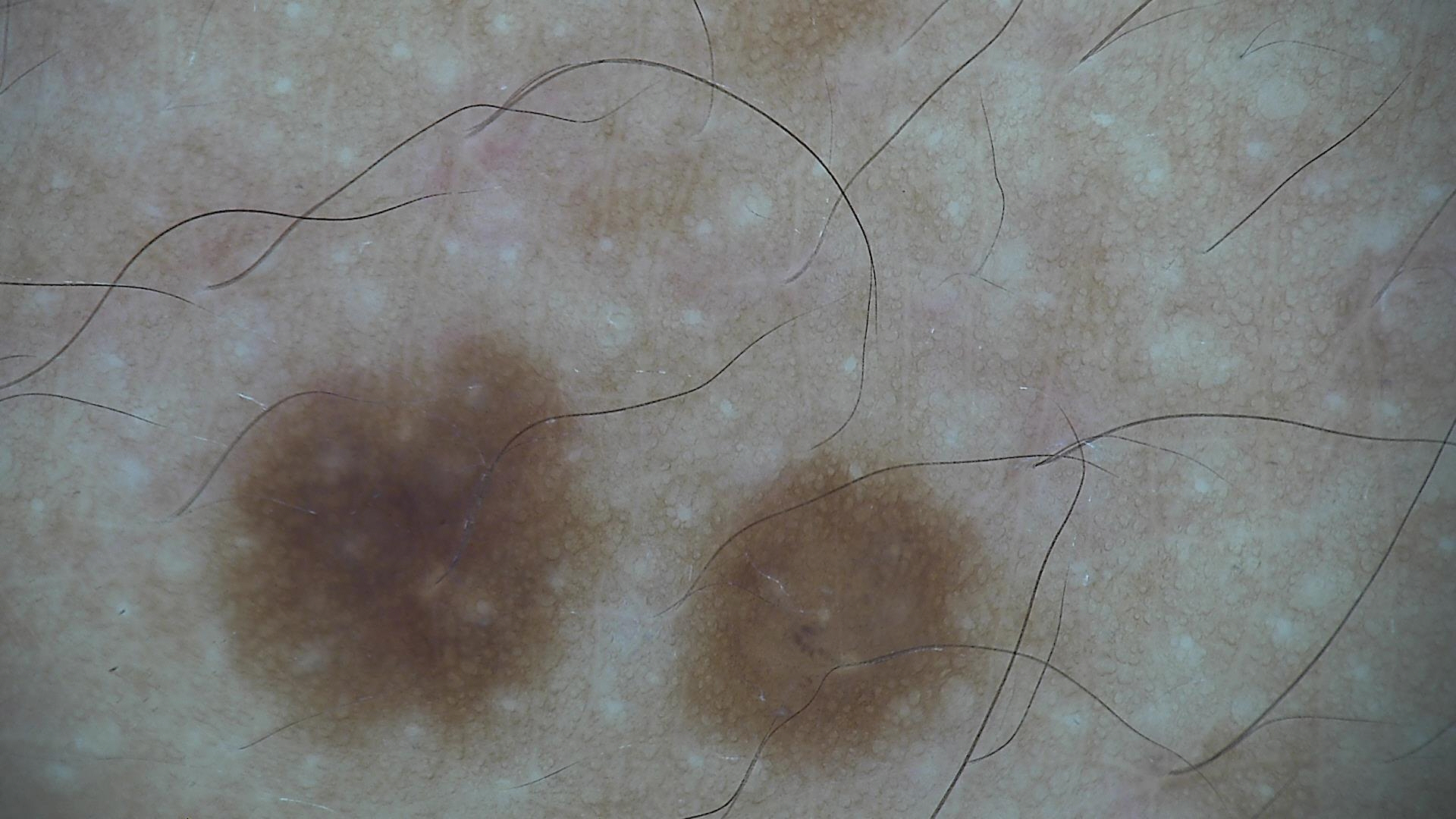A dermoscopic close-up of a skin lesion. The diagnosis was a benign lesion — a dysplastic junctional nevus.